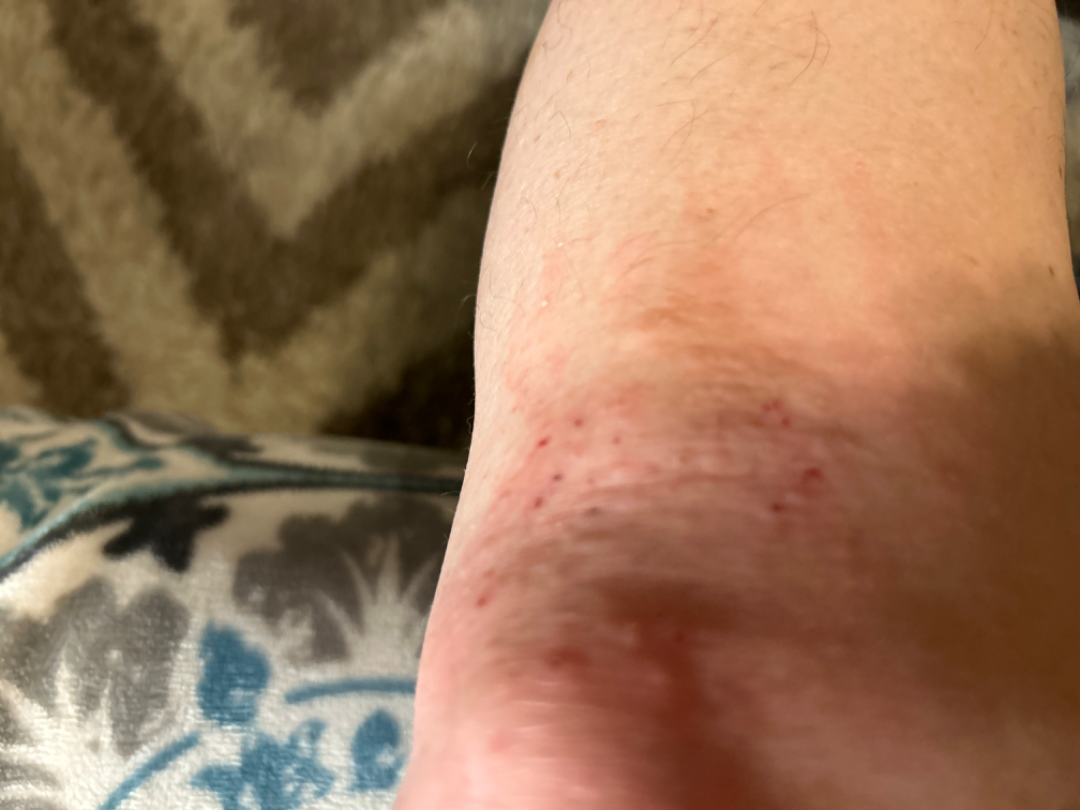{
  "systemic_symptoms": "none reported",
  "patient_category": "a rash",
  "shot_type": "close-up",
  "texture": "raised or bumpy",
  "differential": {
    "tied_lead": [
      "Eczema",
      "Dermatitis herpetiformis"
    ]
  }
}